A clinical close-up photograph of a skin lesion — 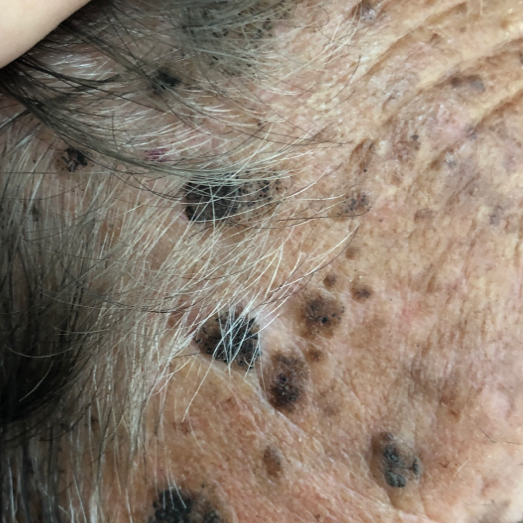Case:
• body site: the face
• reported symptoms: growth, elevation
• assessment: seborrheic keratosis (clinical consensus)